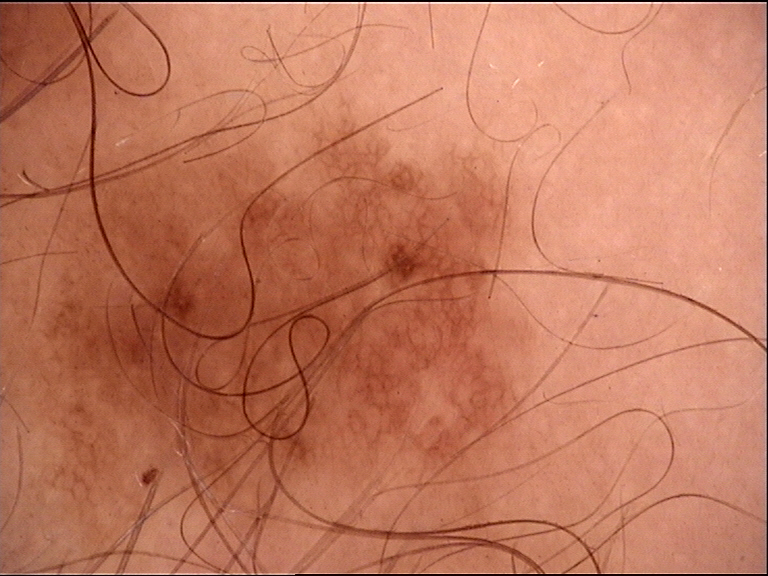A skin lesion imaged with a dermatoscope. The architecture is that of a banal lesion. Diagnosed as a congenital junctional nevus.